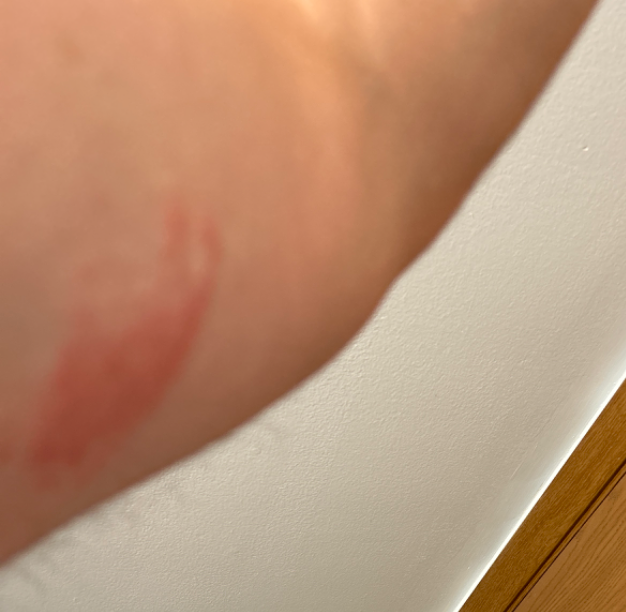  assessment: unable to determine